A dermatoscopic image of a skin lesion: 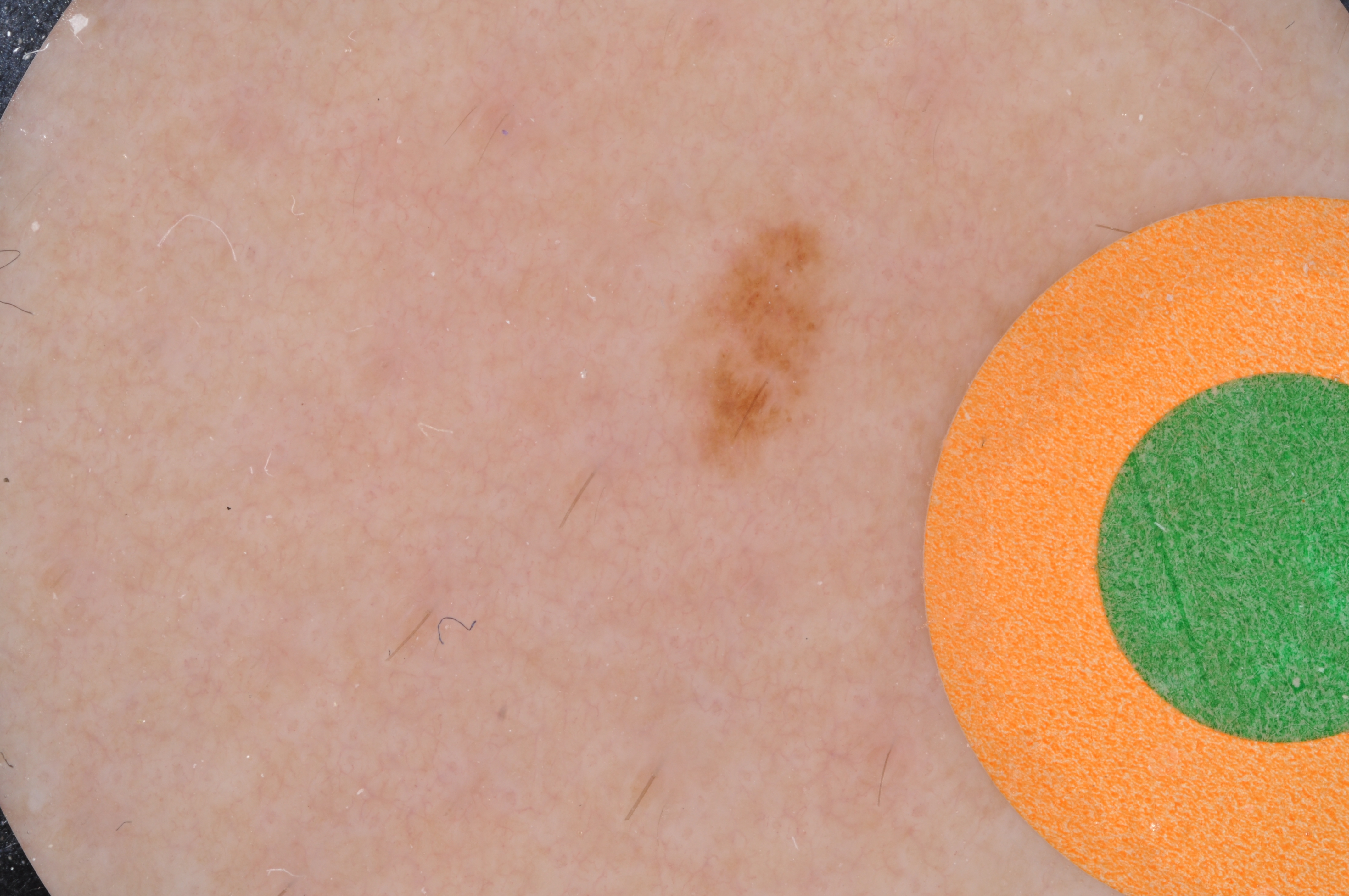The dermoscopic pattern shows no milia-like cysts, negative network, globules, streaks, or pigment network.
With coordinates (x1, y1, x2, y2), the lesion spans box(666, 199, 847, 485).
Consistent with a melanocytic nevus.